The patient reported no systemic symptoms · this image was taken at an angle · the leg is involved — 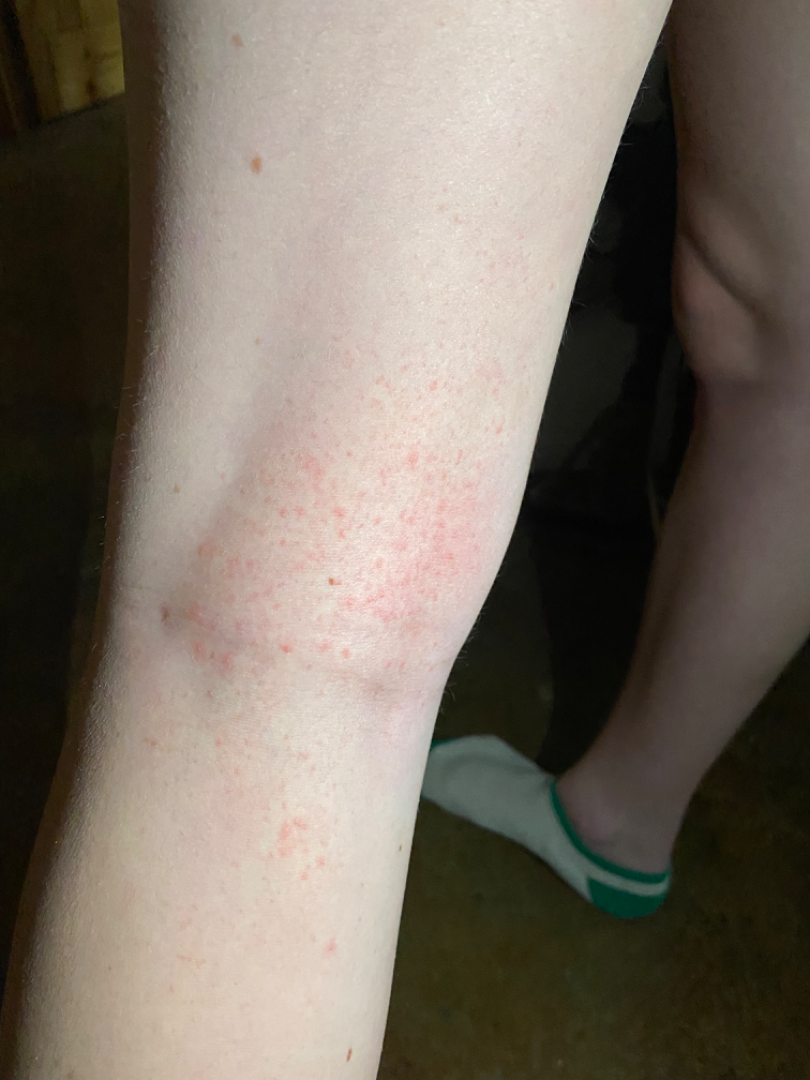Impression:
The reviewing clinician's impression was: Eczema (favored).